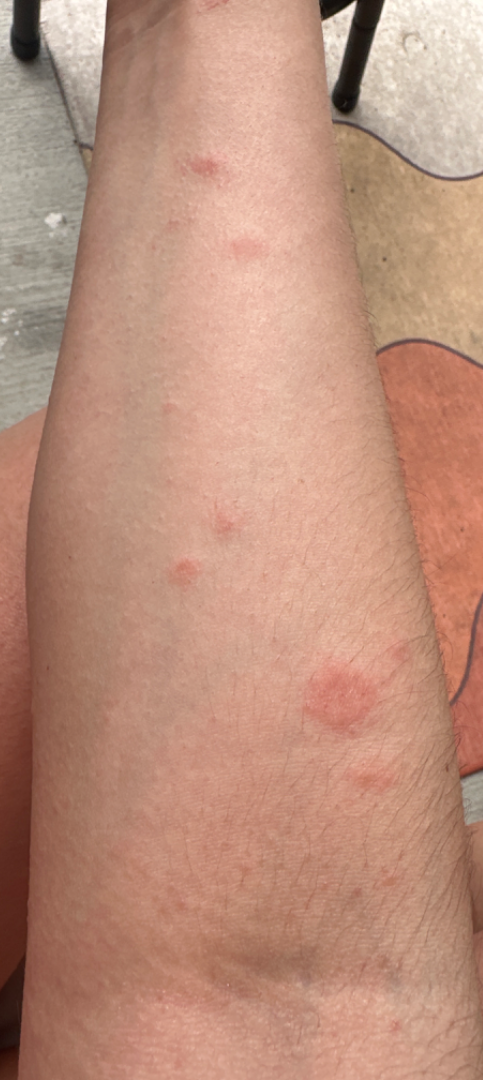Patient information: The front of the torso, head or neck, leg, back of the hand, back of the torso and arm are involved. Close-up view. The patient considered this a rash. The patient reports the lesion is raised or bumpy and rough or flaky. Review: A single dermatologist reviewed the case: consistent with Eczema.